A dermoscopy image of a single skin lesion.
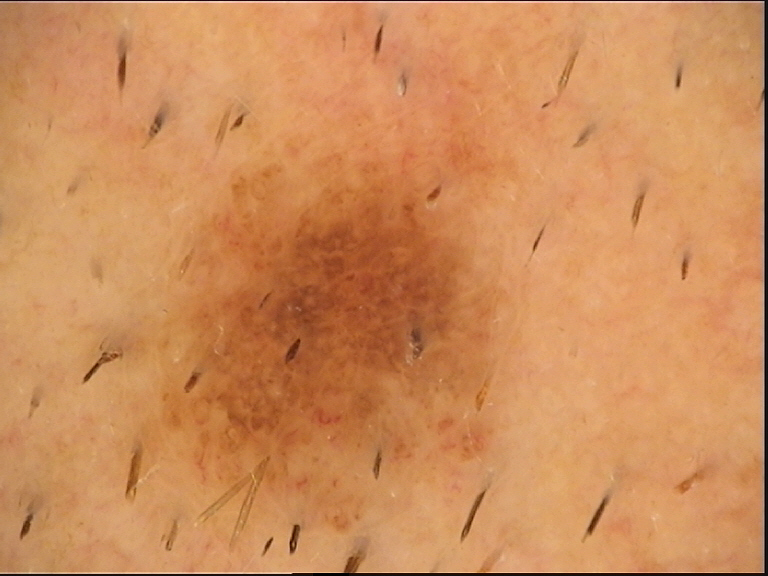Labeled as a dysplastic junctional nevus.